A dermoscopy image of a single skin lesion:
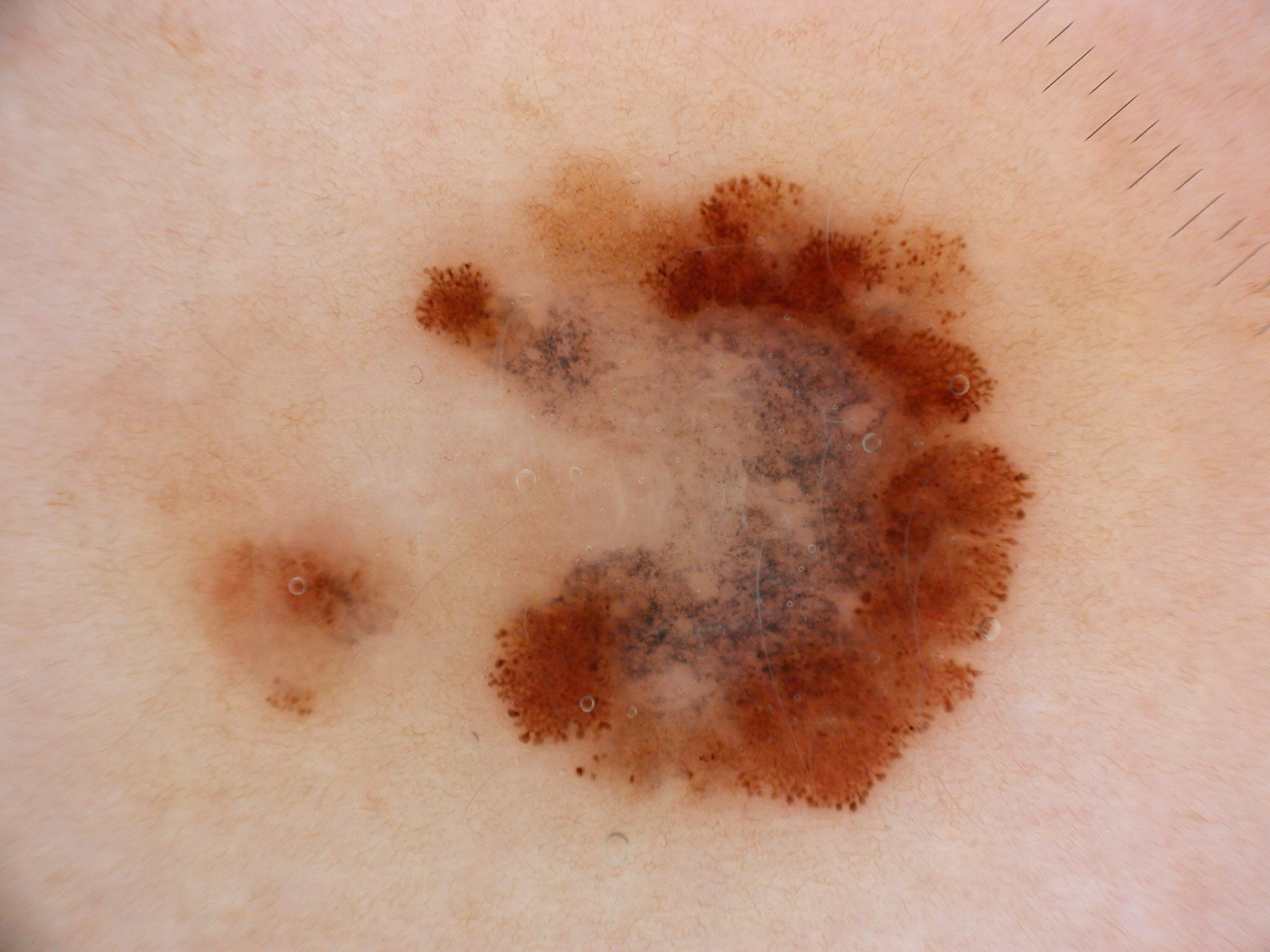In (x1, y1, x2, y2) order, the visible lesion spans box(177, 145, 1038, 819).
Dermoscopically, the lesion shows pigment network, streaks, and globules, with no negative network or milia-like cysts.
On biopsy, the diagnosis was a melanoma, a malignancy.